The photograph was taken at a distance; female subject, age 40–49; located on the head or neck:
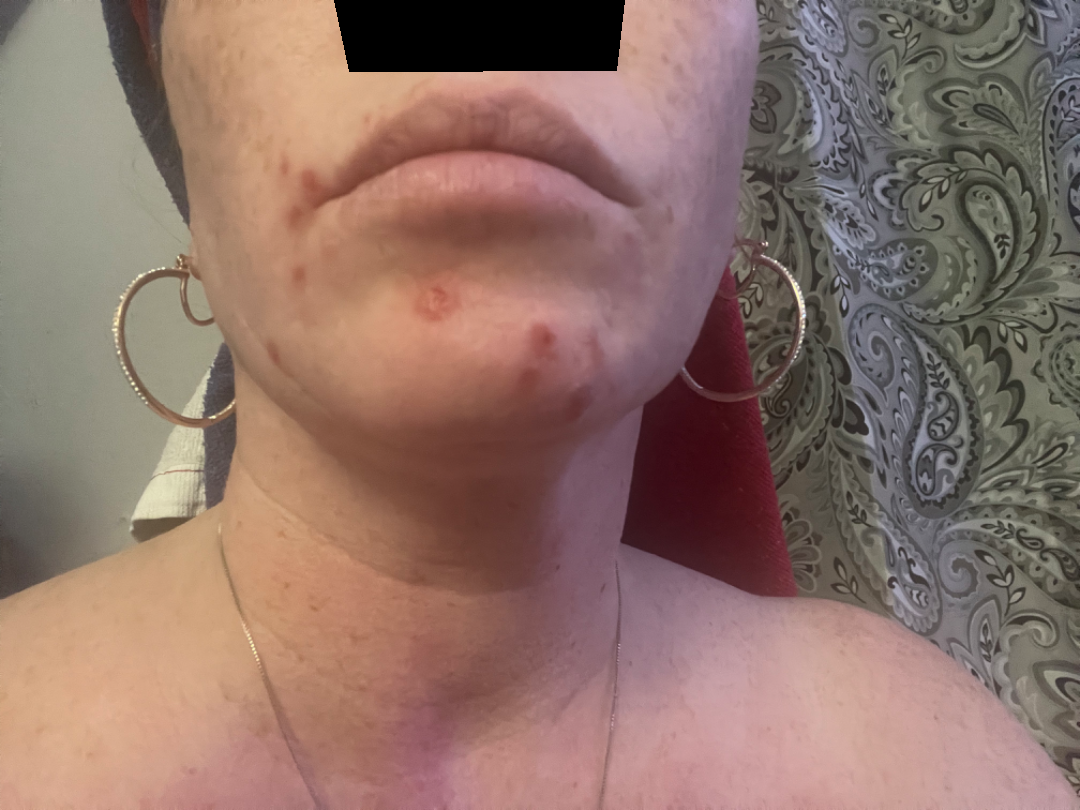* impression: most consistent with Acne